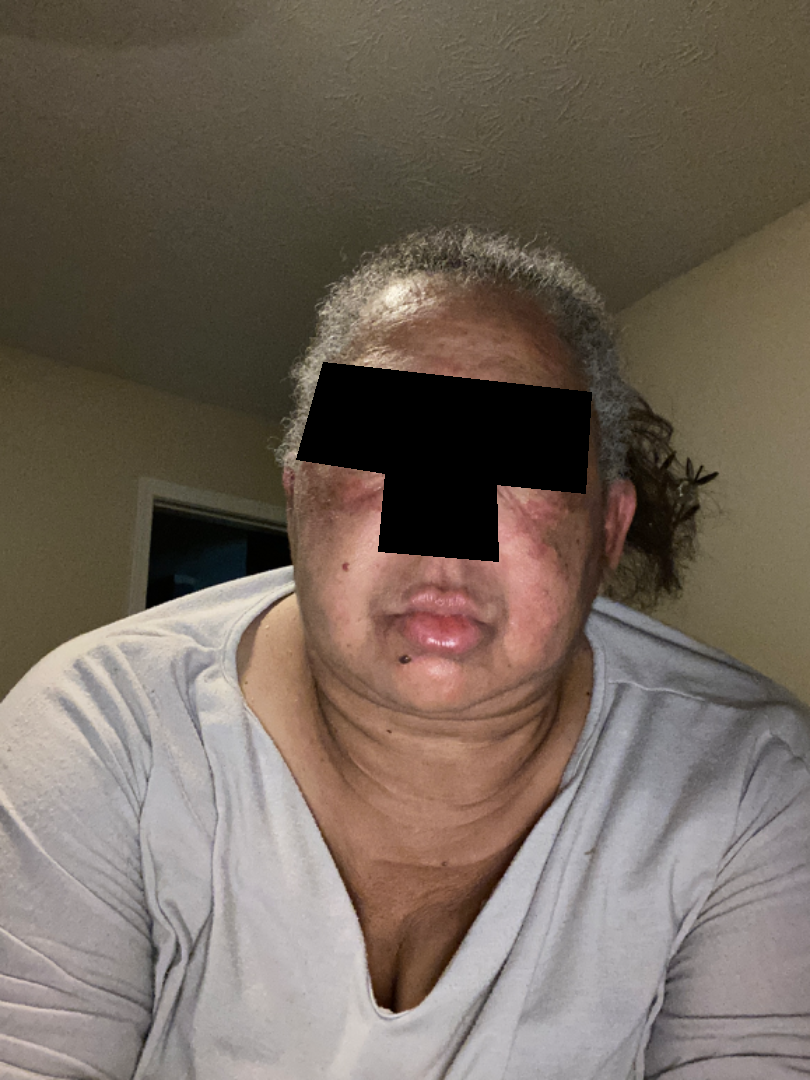{"symptoms": "itching", "patient_category": "a rash", "skin_tone": {"fitzpatrick": "V"}, "duration": "one to three months", "shot_type": "at a distance", "patient": "female, age 60–69", "body_site": "head or neck", "texture": ["fluid-filled", "flat", "rough or flaky", "raised or bumpy"], "differential": {"tied_lead": ["Seborrheic Dermatitis", "Eczema"], "unlikely": ["Cutaneous lupus", "Allergic Contact Dermatitis", "Rosacea"]}}